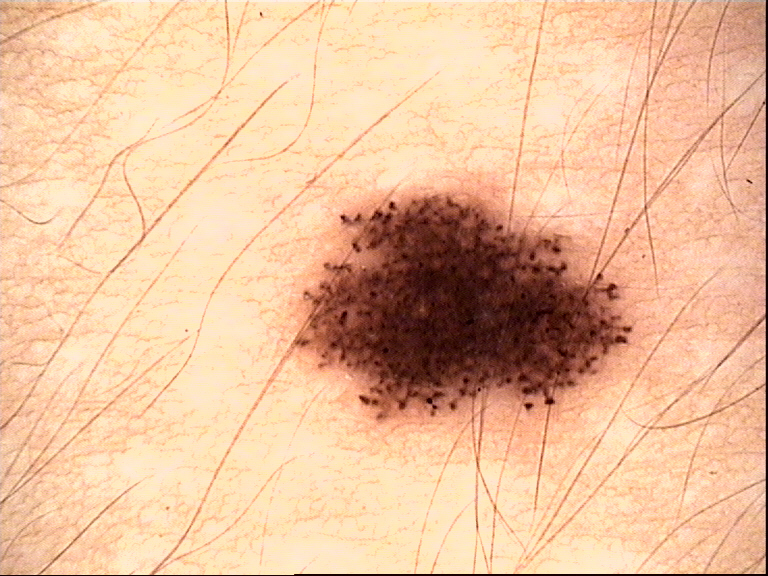Conclusion: The diagnosis was a dysplastic junctional nevus.